The condition has been present for less than one week · the subject is a female aged 40–49 · the patient indicates itching · skin tone: FST II · the patient indicates the lesion is raised or bumpy · the arm is involved · an image taken at an angle:
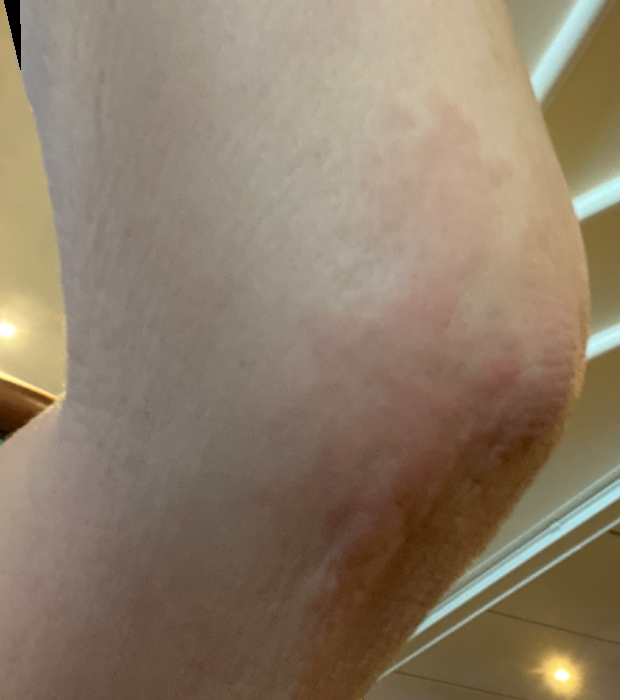  differential:
    Allergic Contact Dermatitis: 0.41
    Urticaria: 0.27
    Eczema: 0.23
    Dermatitis herpetiformis: 0.09